A female patient 66 years of age. A clinical photograph showing a skin lesion.
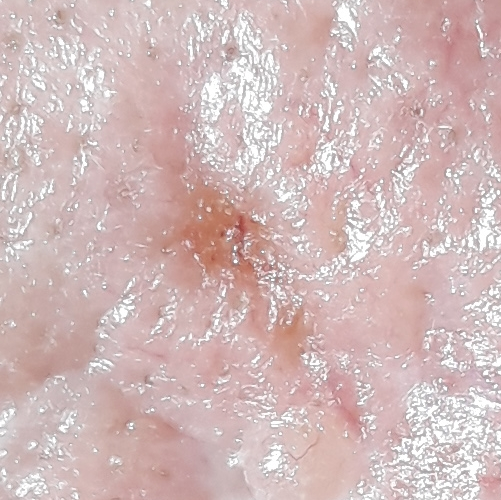Case:
- location — the nose
- symptoms — elevation / no itching, no pain
- pathology — basal cell carcinoma (biopsy-proven)